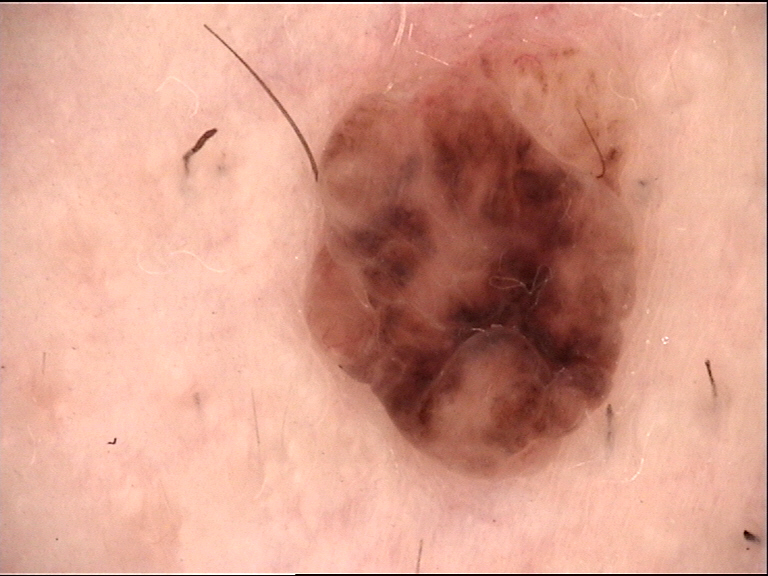category: banal
diagnosis: dermal nevus (expert consensus)